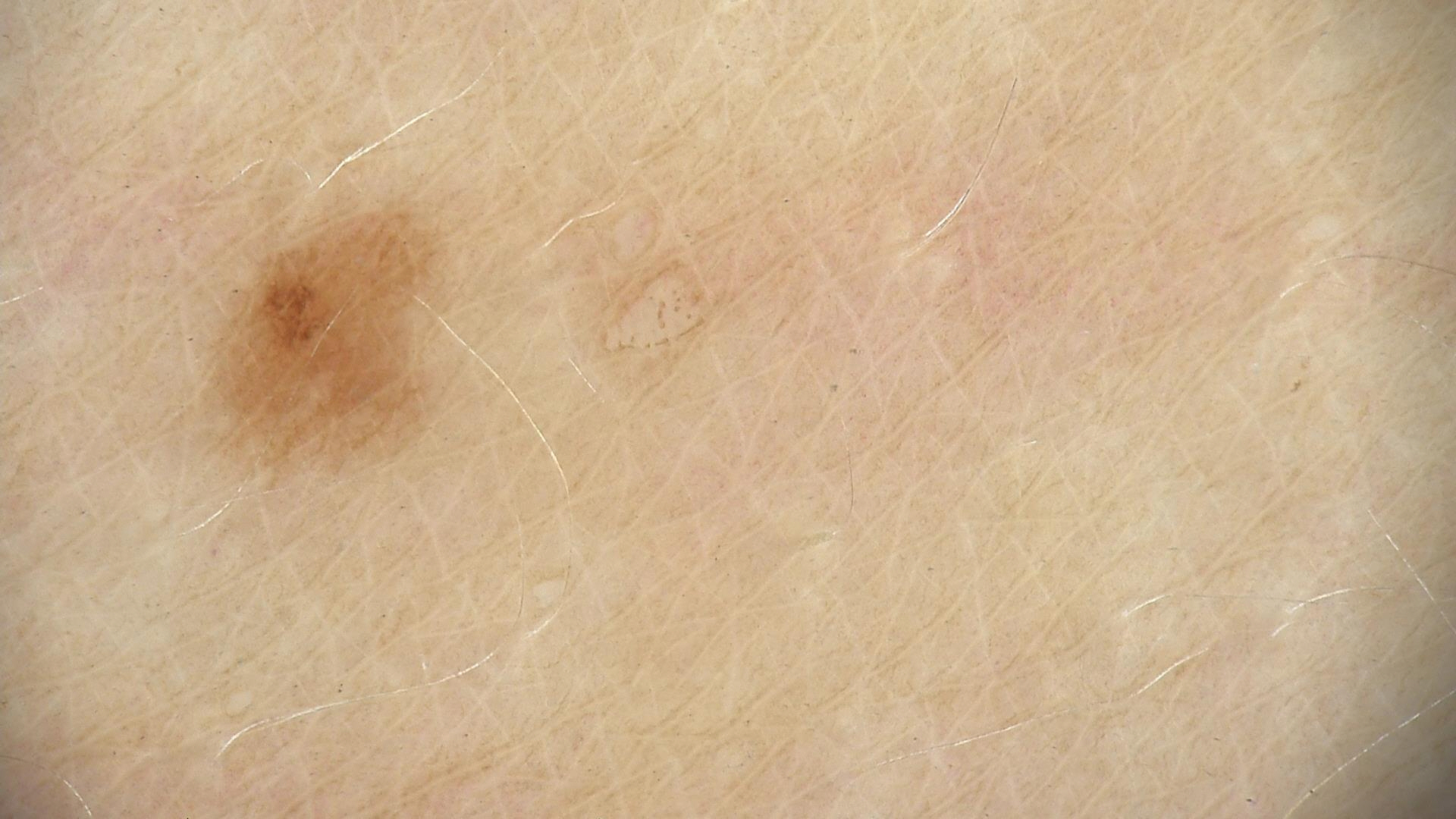Summary: A dermoscopic image of a skin lesion. Impression: The diagnosis was a benign lesion — a dysplastic junctional nevus.